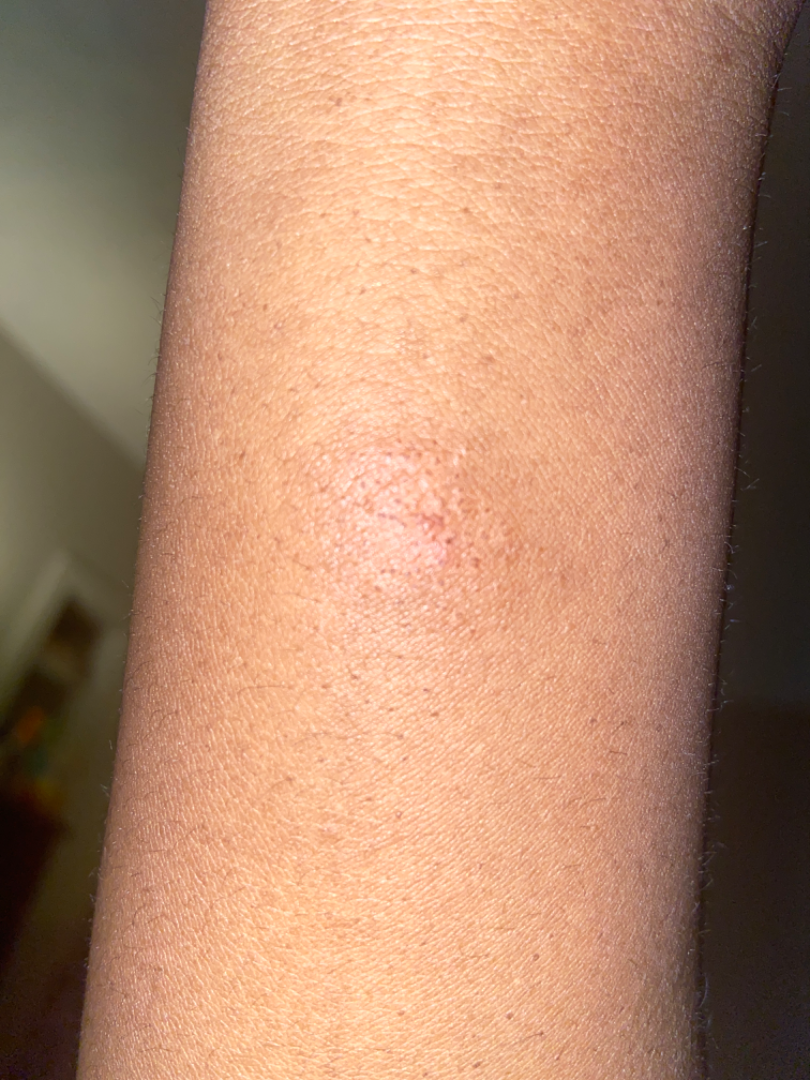Impression: The differential includes Abscess, Impetigo and Insect Bite, with no clear leading consideration.